A dermoscopic close-up of a skin lesion.
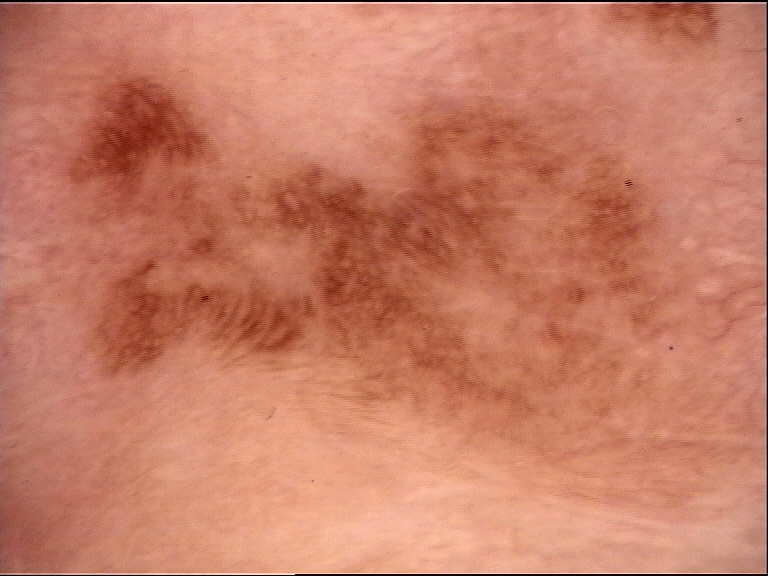The morphology is that of a dysplastic lesion.
The diagnostic label was a recurrent nevus.